Close-up view · the contributor is 40–49, female · the lesion involves the head or neck.
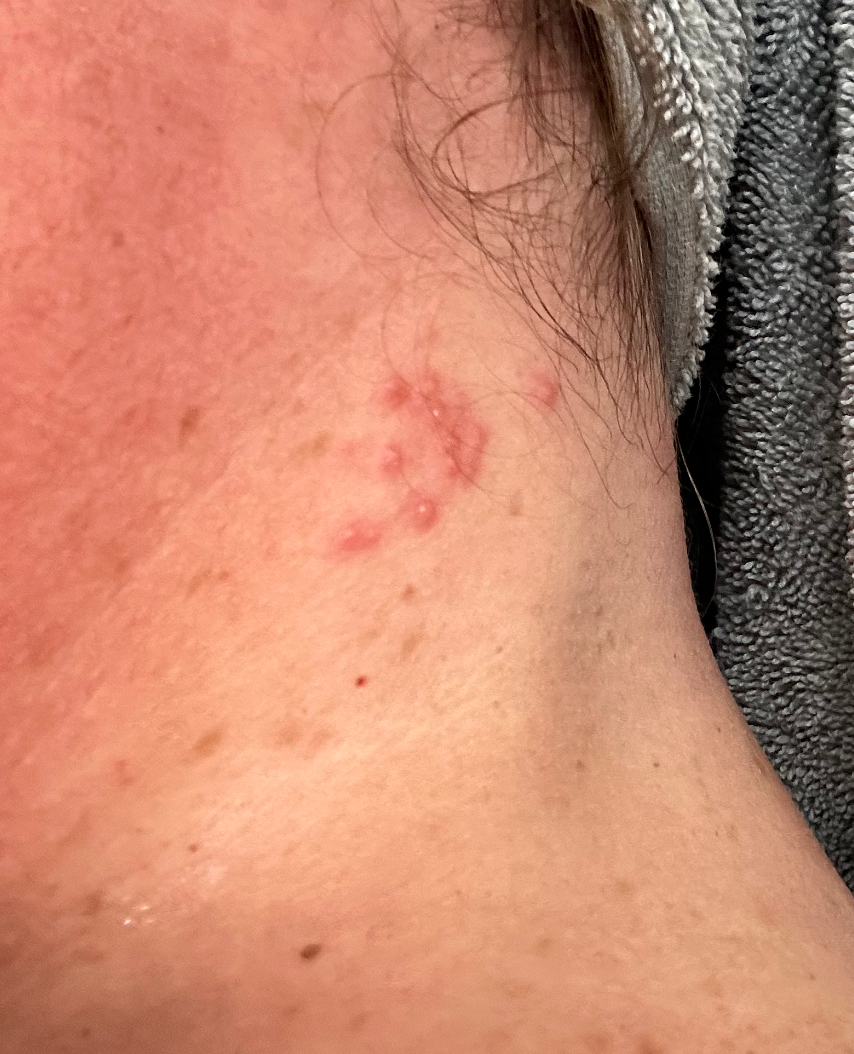systemic_symptoms: none reported
duration: less than one week
texture:
  - raised or bumpy
  - fluid-filled
differential:
  leading:
    - Herpes Simplex
  considered:
    - Folliculitis